The photo was captured at a distance; the arm is involved; the patient indicates itching; the patient considered this a rash; skin tone: human graders estimated Monk skin tone scale 2; the patient indicates the condition has been present for one to four weeks; the patient indicates the lesion is rough or flaky; the patient reported no systemic symptoms — 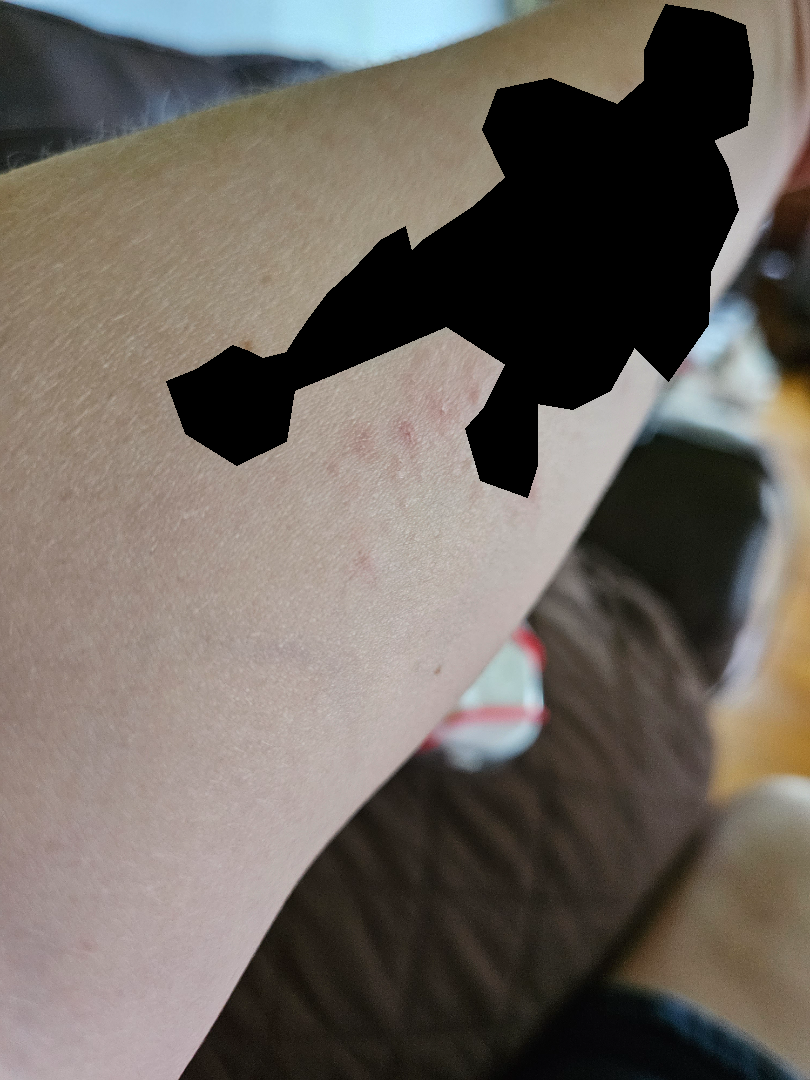{
  "assessment": "not assessable"
}